A close-up photograph — 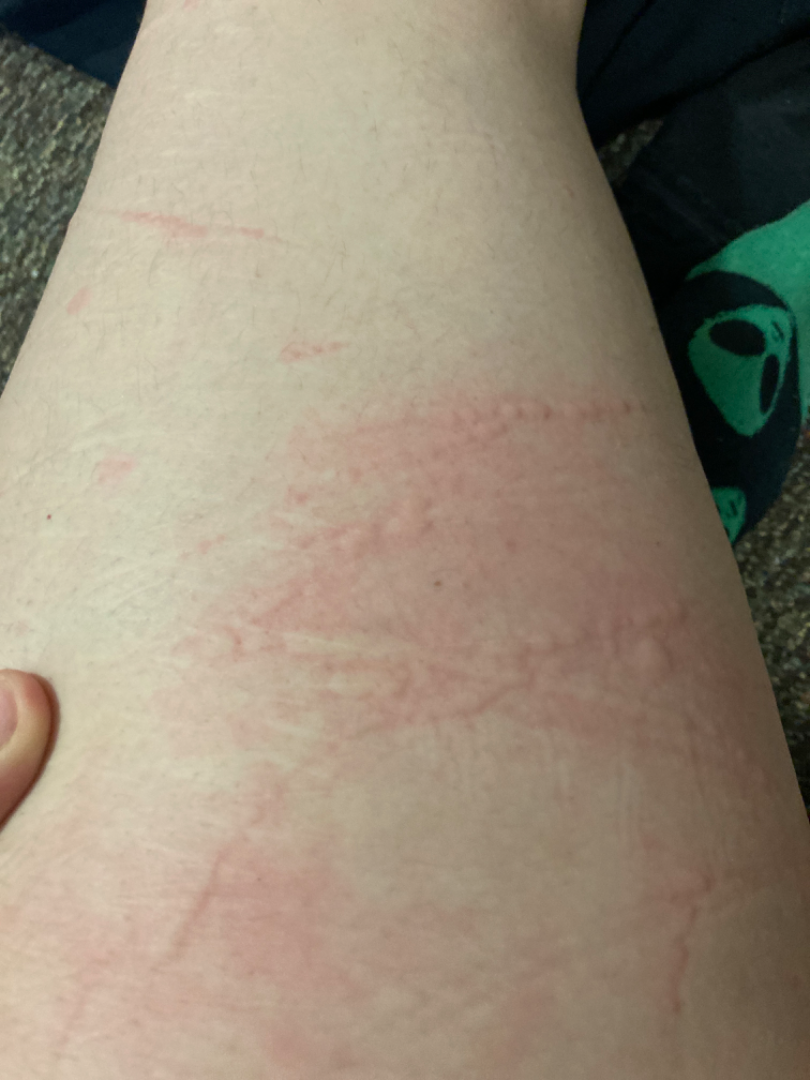Q: What conditions are considered?
A: reviewed remotely by one dermatologist: most consistent with Urticaria; the differential also includes Eczema